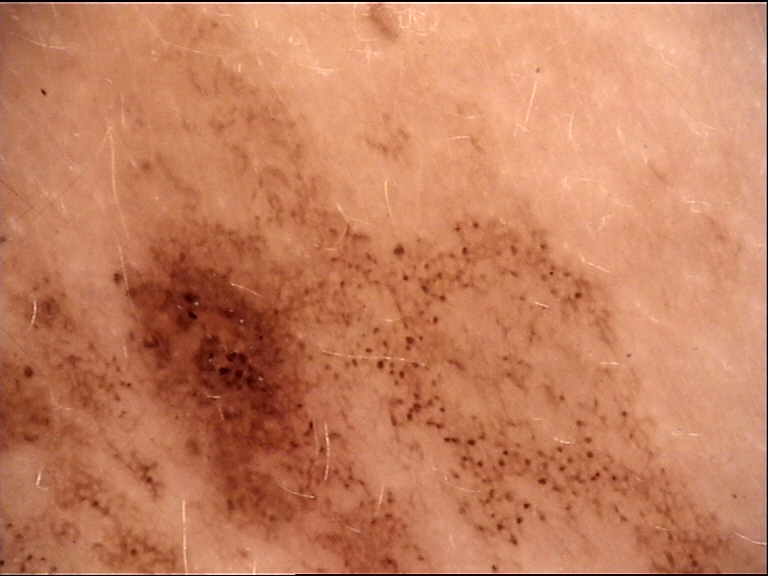The morphology is that of a banal lesion. Classified as a congenital junctional nevus.